The photograph is a close-up of the affected area · FST III; lay reviewers estimated Monk skin tone scale 1 or 4 (two reviewer pools disagreed): 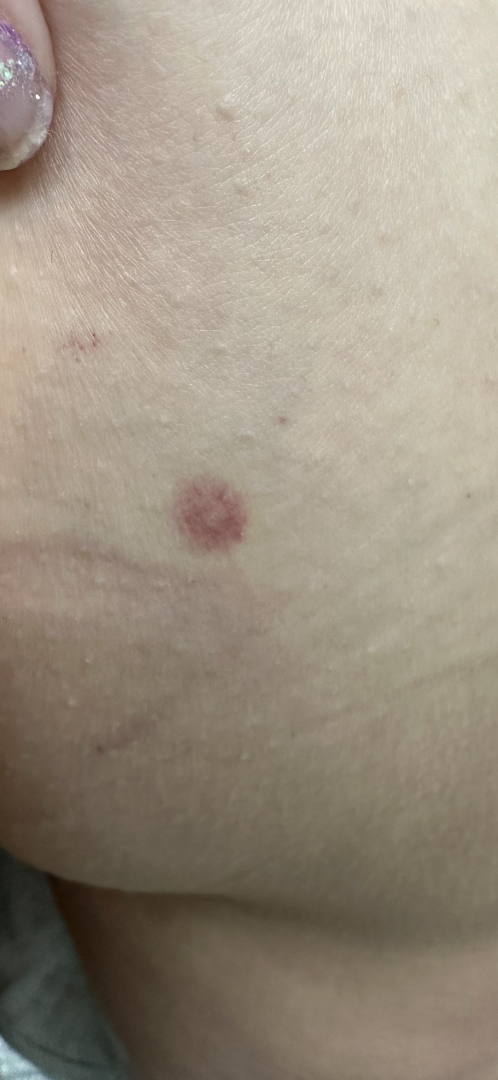Findings:
– assessment · could not be assessed